The lesion involves the arm; the photograph is a close-up of the affected area — 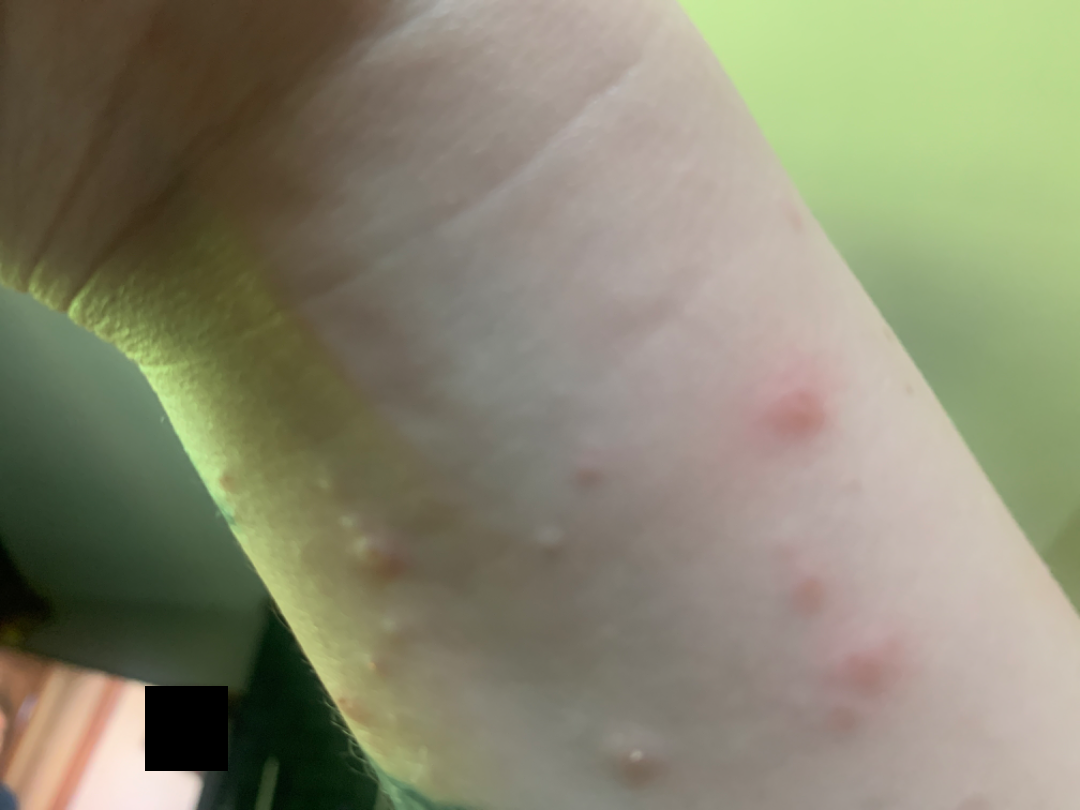Q: Could the case be diagnosed?
A: indeterminate